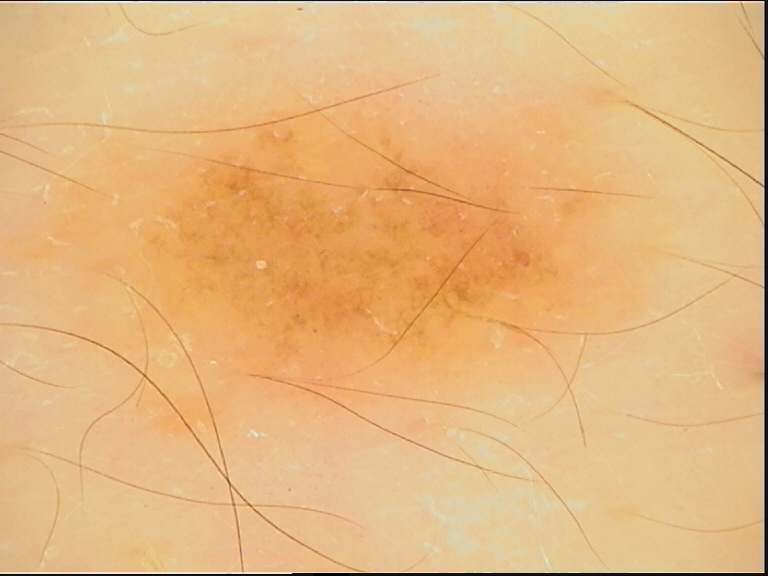Q: What is the imaging modality?
A: dermatoscopy
Q: What was the diagnostic impression?
A: dysplastic junctional nevus (expert consensus)